Recorded as Fitzpatrick skin type III; a female patient in their early 80s; a smartphone photograph of a skin lesion; history notes prior skin cancer (patient or family).
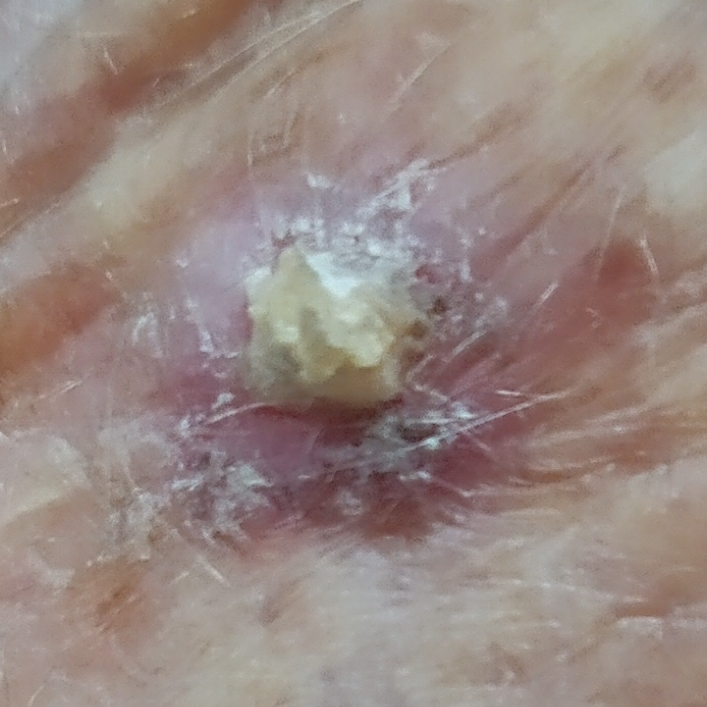region = a forearm; diameter = 10x7 mm; symptoms = itching, elevation; pathology = actinic keratosis (biopsy-proven).